The subject is 18–29, female. The affected area is the back of the torso. The patient indicates the condition has been present for less than one week. Close-up view. Fitzpatrick II; lay reviewers estimated MST 2. No relevant lesion symptoms reported. The patient considered this a rash.
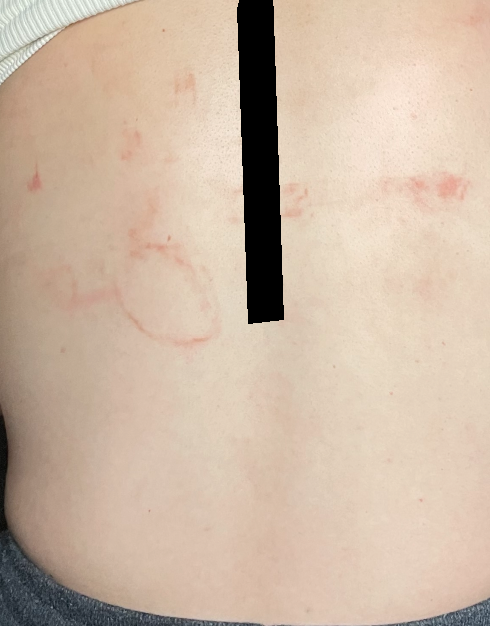The image was not sufficient for the reviewer to characterize the skin condition.